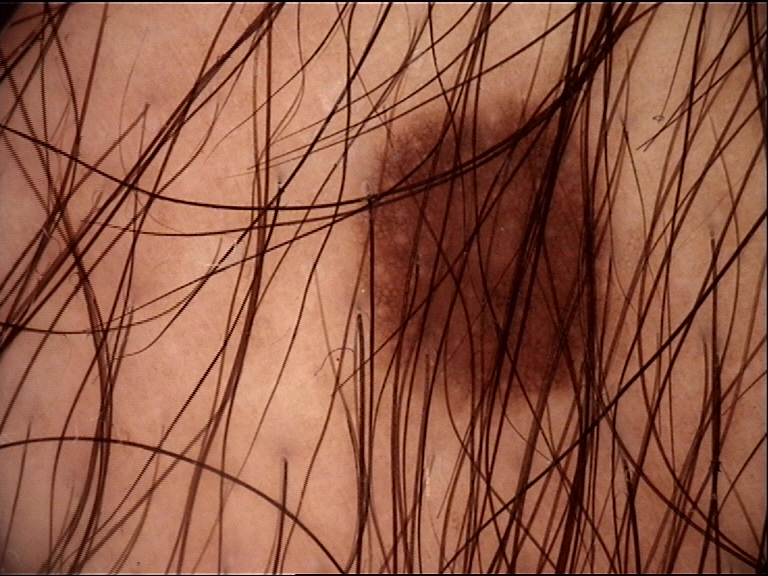modality: dermatoscopy
diagnostic label: junctional nevus (expert consensus)